The leg is involved. Close-up view. The subject is 18–29, female — 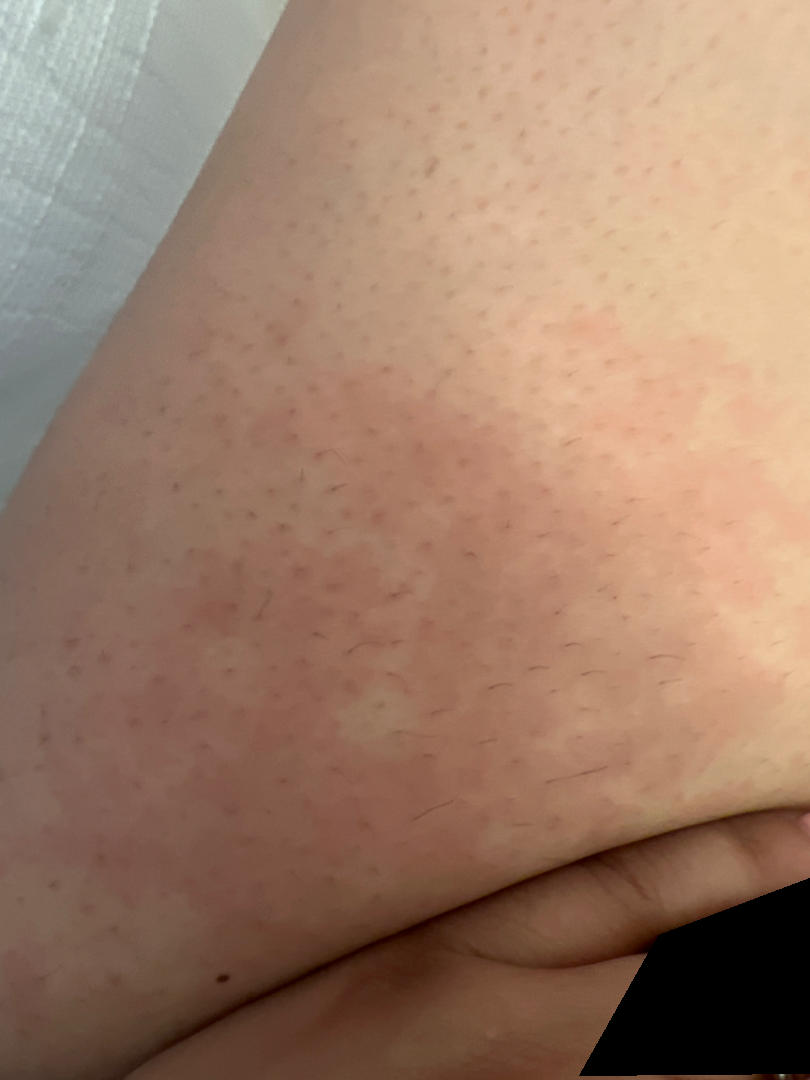Q: What is the lesion texture?
A: raised or bumpy
Q: When did this start?
A: one to three months
Q: Reported symptoms?
A: darkening and itching
Q: What is the differential diagnosis?
A: three dermatologists each reviewed the case: in keeping with Urticaria